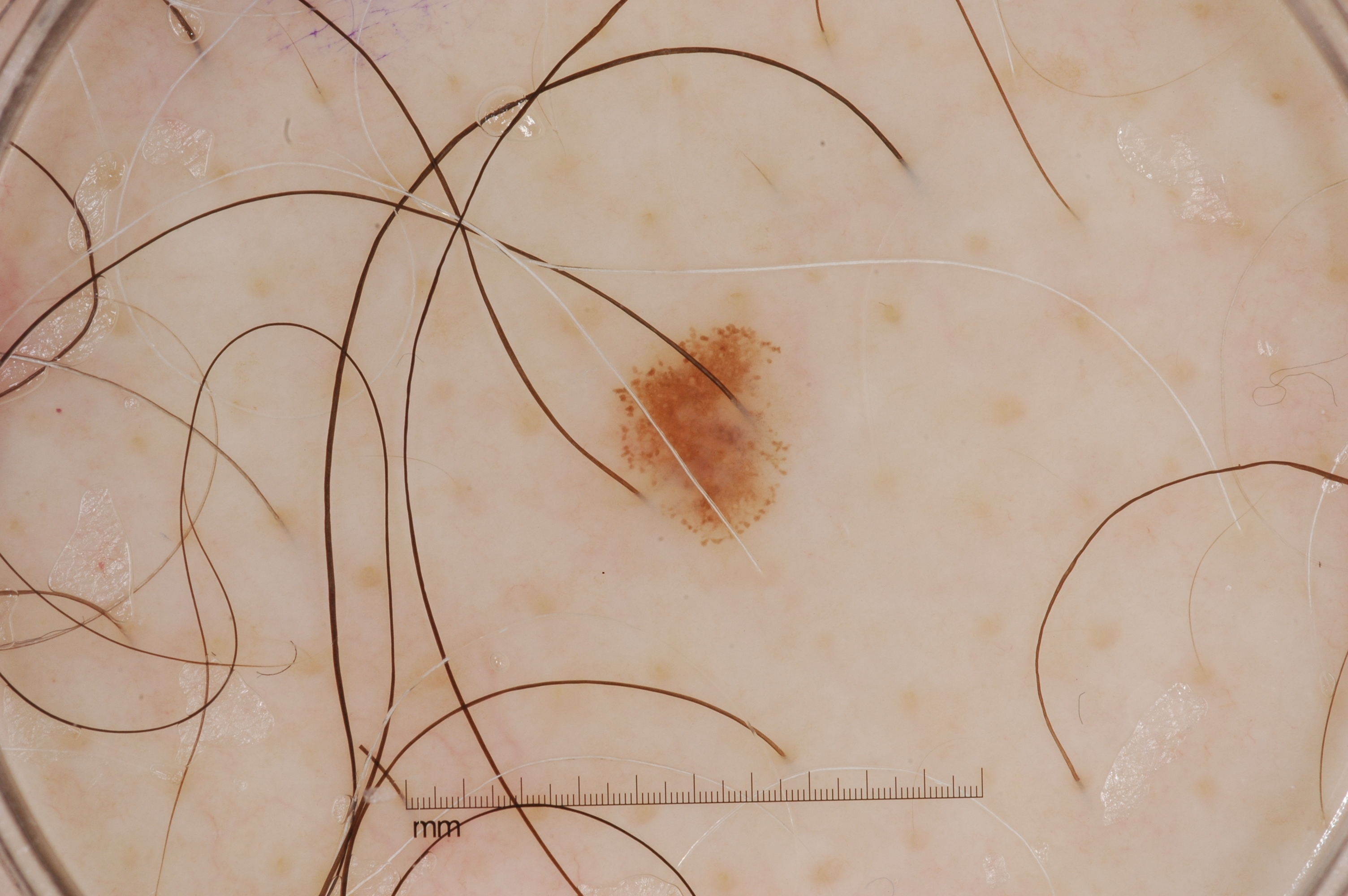modality — dermatoscopic image of a skin lesion
subject — male, aged 53 to 57
lesion bbox — left=611, top=322, right=779, bottom=539
lesion size — ~2% of the field
dermoscopic features — streaks; absent: pigment network, milia-like cysts, and negative network
impression — a melanocytic nevus